The lesion involves the arm. This is a close-up image.
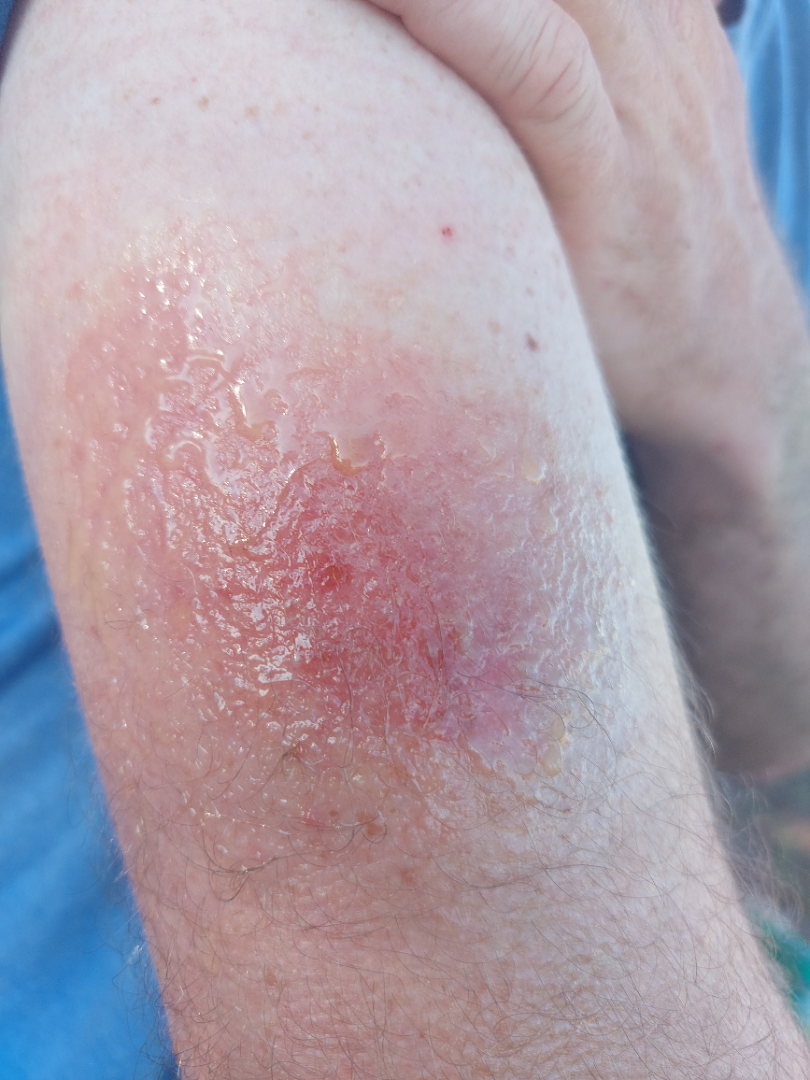The patient described the issue as a rash. Reported duration is one to four weeks. Texture is reported as raised or bumpy. Acute dermatitis, NOS (considered); Allergic Contact Dermatitis (considered).